A dermoscopy image of a single skin lesion · a female subject approximately 50 years of age — 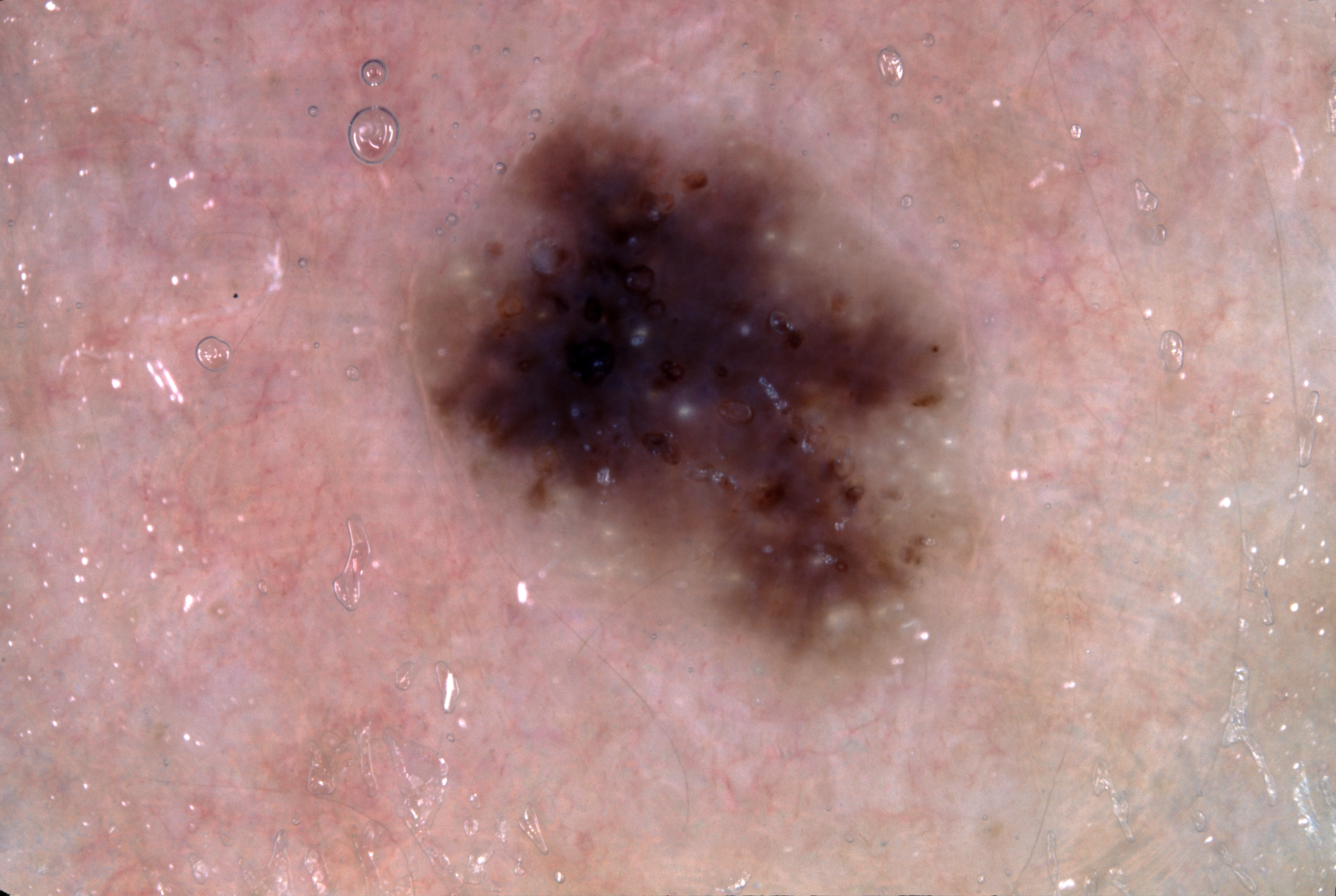Summary: The lesion is bounded by <bbox>418, 119, 960, 672</bbox>. Dermoscopic assessment notes milia-like cysts. Conclusion: The lesion was assessed as a seborrheic keratosis, a benign skin lesion.